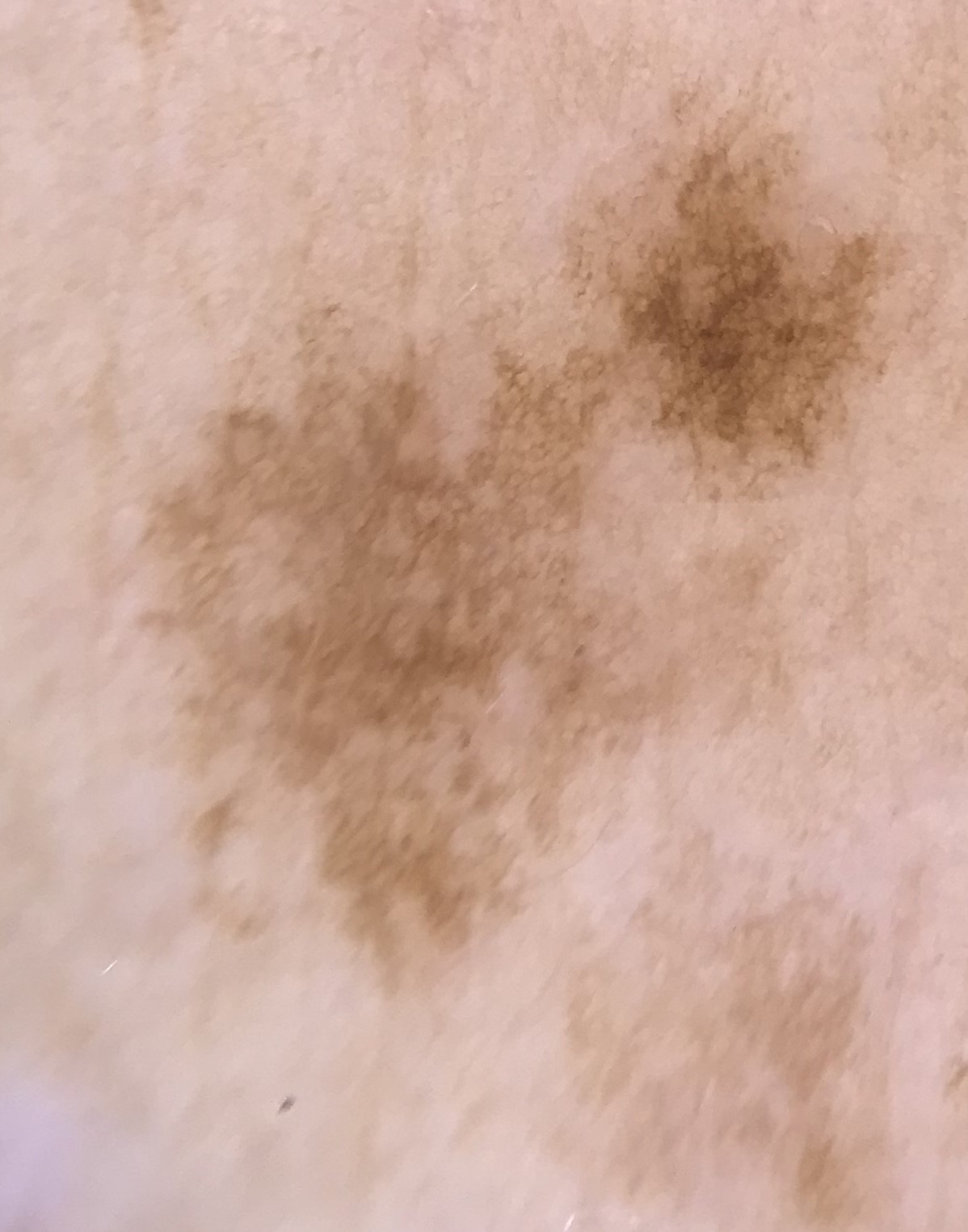Dermoscopy of a skin lesion.
Labeled as a solar lentigo.